The photograph is a close-up of the affected area:
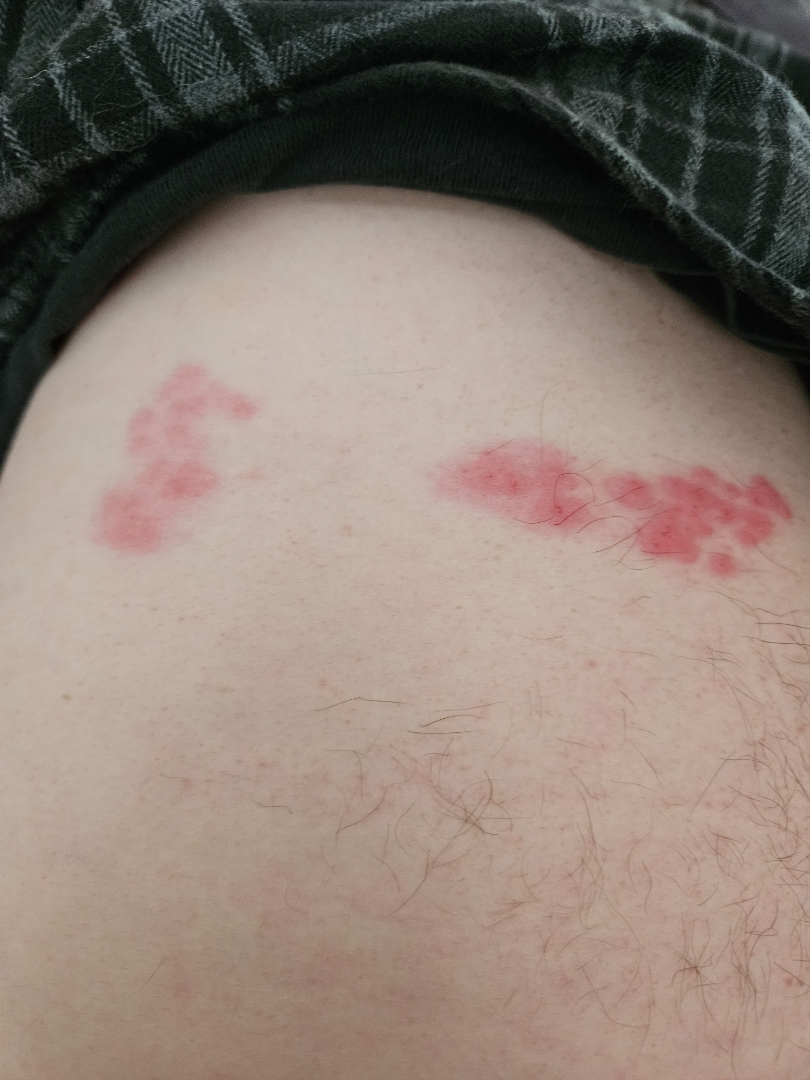Q: What conditions are considered?
A: reviewed remotely by one dermatologist: in keeping with Herpes Zoster